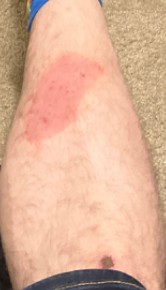The image was not sufficient for the reviewer to characterize the skin condition. This image was taken at a distance.